Close-up view · skin tone: lay reviewers estimated a Monk Skin Tone of 3 · the patient is female · the lesion is described as rough or flaky · the head or neck and leg are involved: 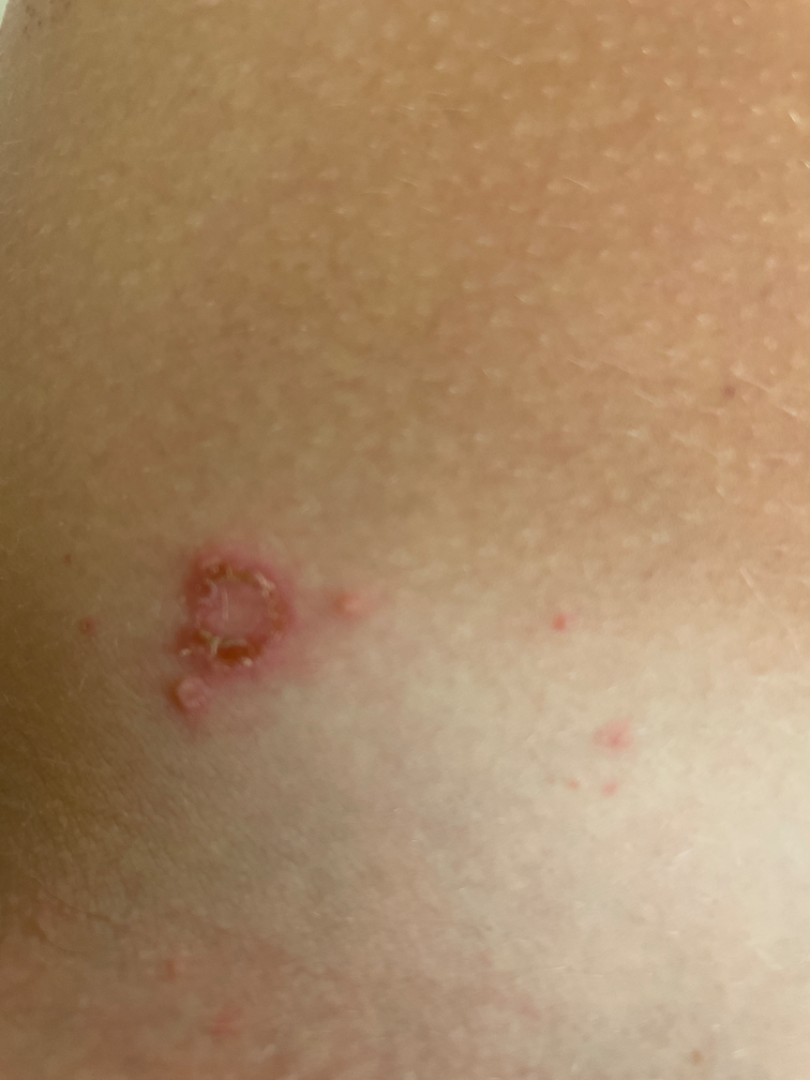| key | value |
|---|---|
| assessment | unable to determine |